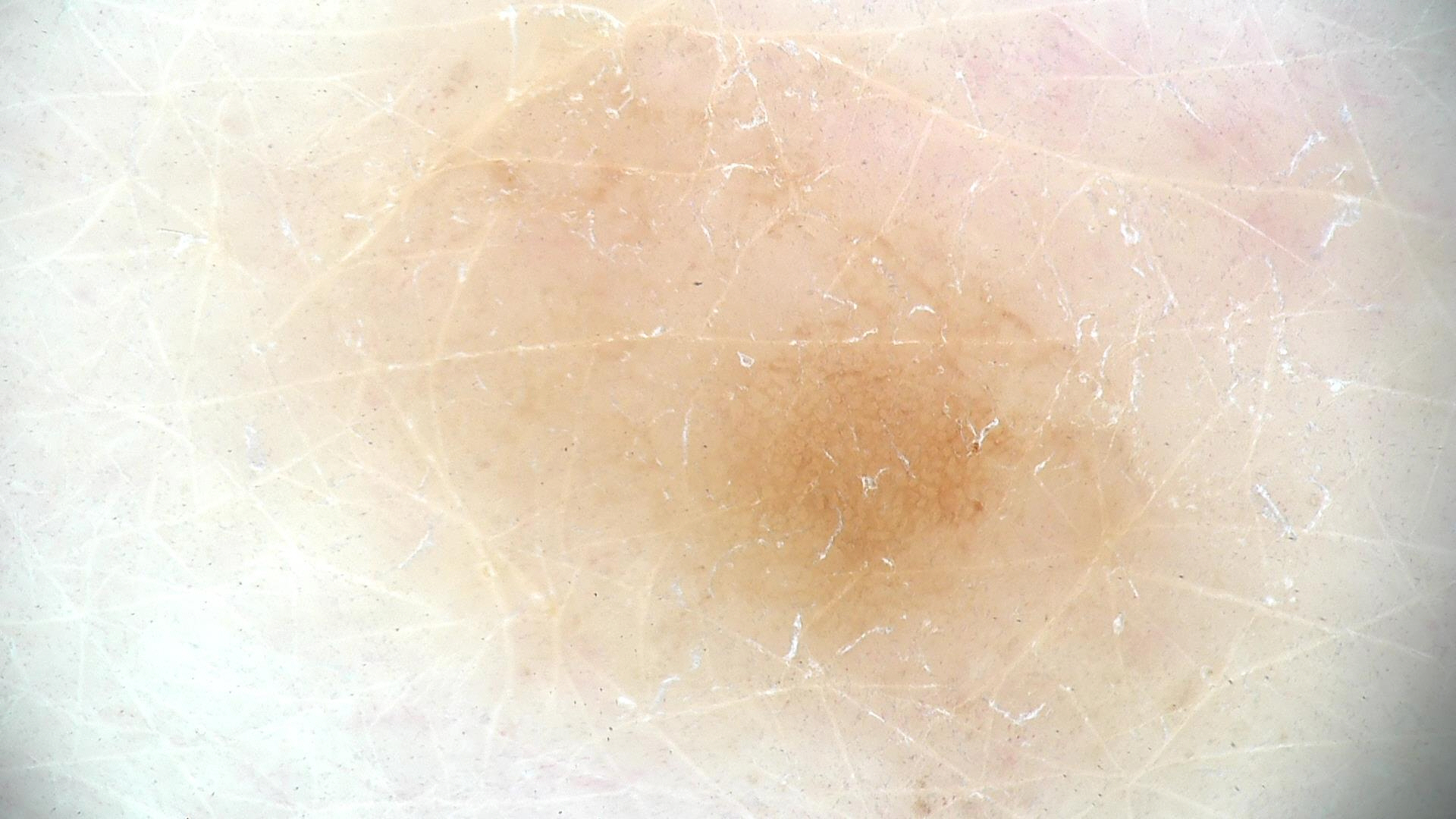Consistent with a banal lesion — a junctional nevus.